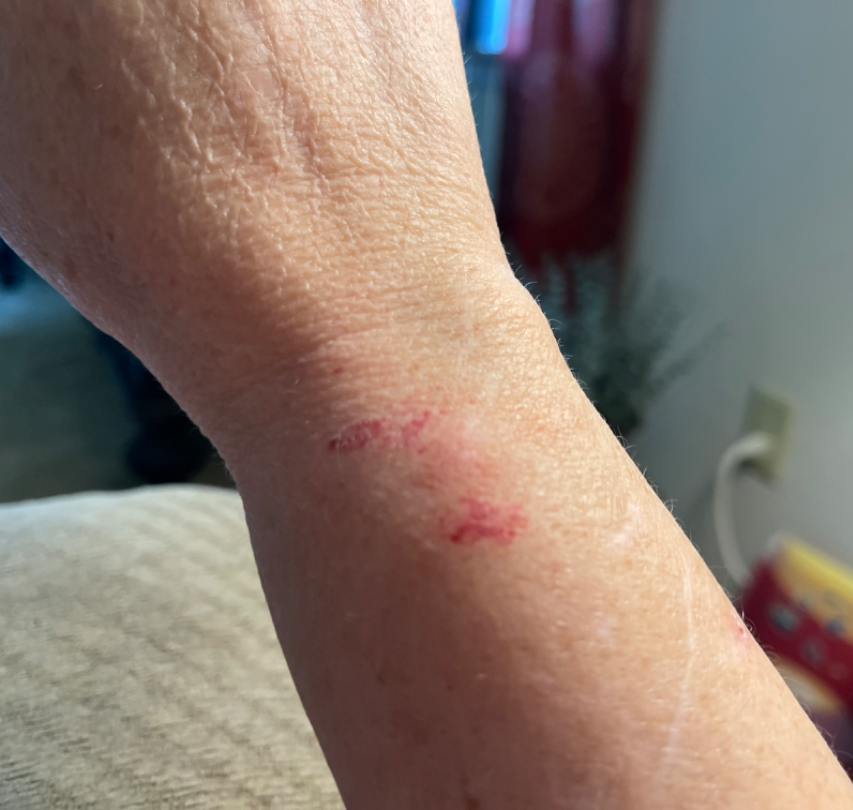{"patient": "female, age 60–69", "shot_type": "close-up", "body_site": "arm", "differential": {"leading": ["Abrasion, scrape, or scab"], "considered": ["Purpura"], "unlikely": ["Eczema"]}}